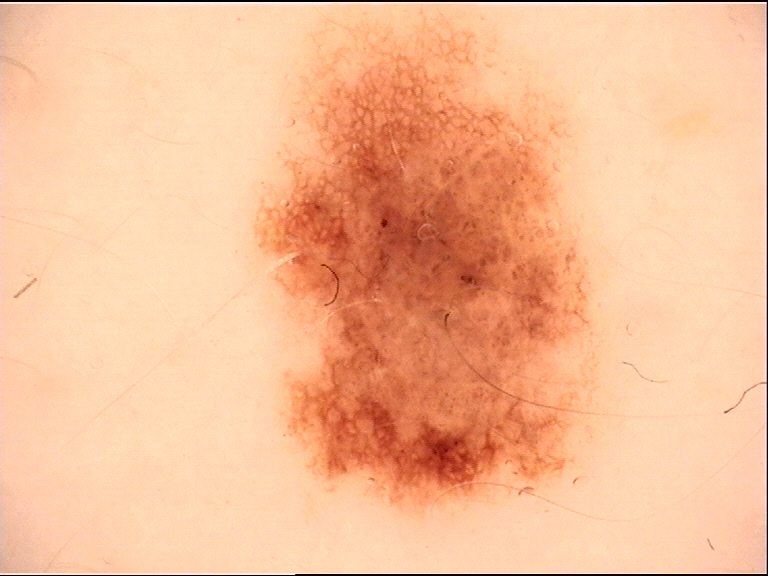image type = dermatoscopy, diagnostic label = dysplastic junctional nevus (expert consensus).